The contributor is 18–29, male · this image was taken at a distance · the lesion involves the back of the torso: 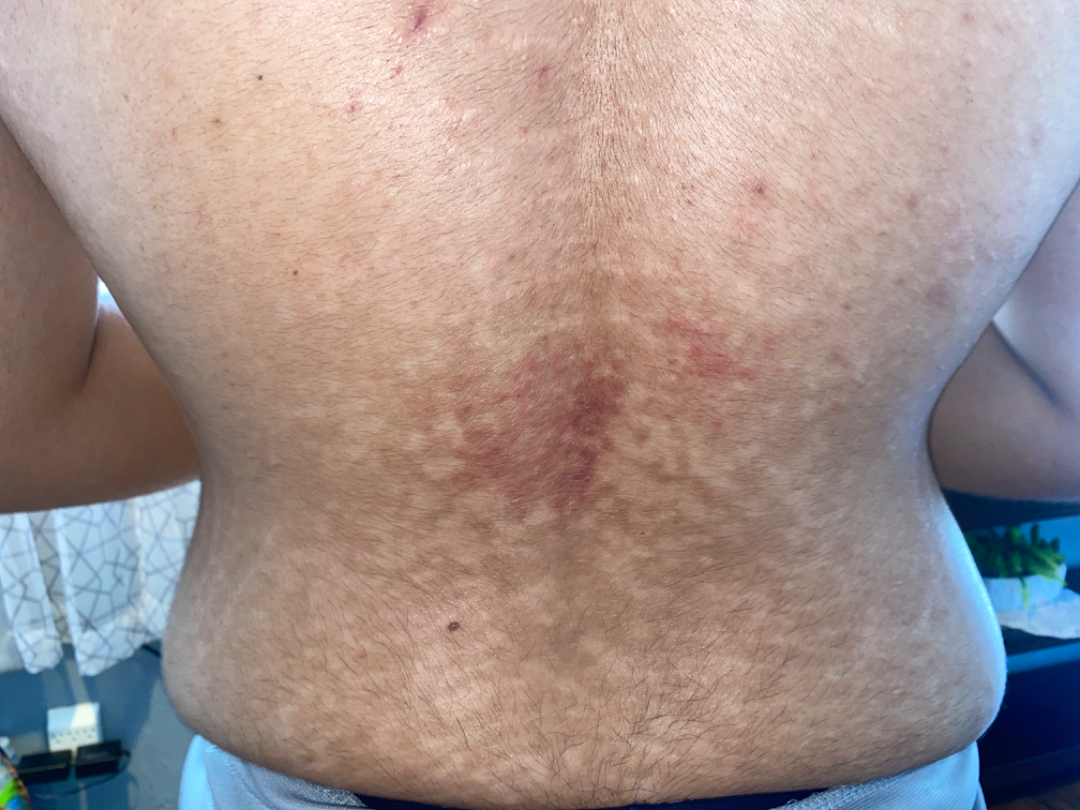Q: How long has this been present?
A: less than one week
Q: Any systemic symptoms?
A: mouth sores
Q: What symptoms does the patient report?
A: itching, enlargement and bothersome appearance
Q: What conditions are considered?
A: the favored diagnosis is Erythema ab igne; also raised was Livedo reticularis